A female patient roughly 70 years of age; a dermoscopic view of a skin lesion: 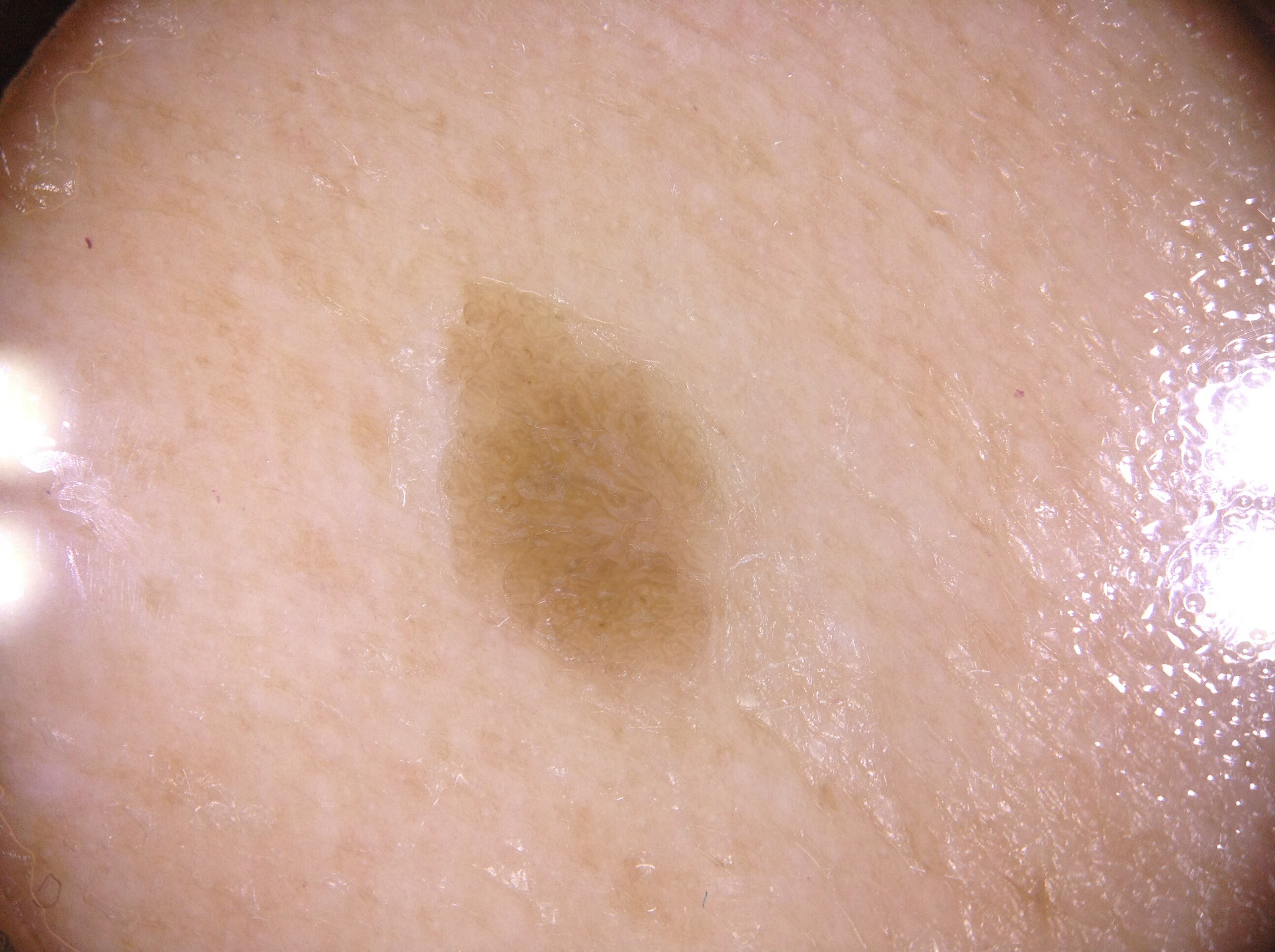<case>
  <dermoscopic_features>
    <present/>
    <absent>negative network, streaks, pigment network, milia-like cysts</absent>
  </dermoscopic_features>
  <lesion_location>
    <bbox_xyxy>458, 320, 707, 669</bbox_xyxy>
  </lesion_location>
  <lesion_extent>small</lesion_extent>
  <diagnosis>
    <name>seborrheic keratosis</name>
    <malignancy>benign</malignancy>
    <lineage>keratinocytic</lineage>
    <provenance>clinical</provenance>
  </diagnosis>
</case>